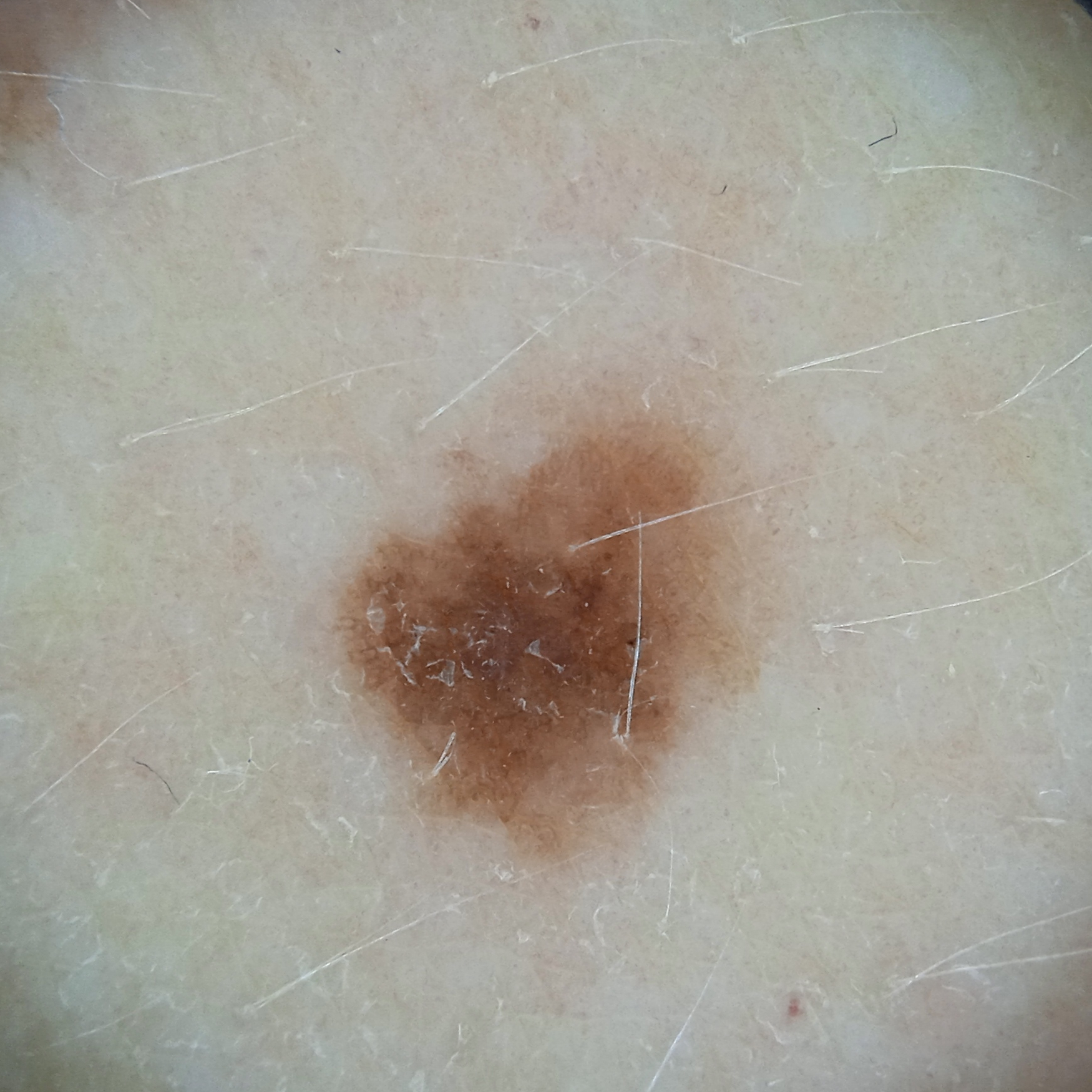* risk factors: a personal history of skin cancer
* modality: dermoscopy
* sun reaction: skin reddens with sun exposure
* patient: female, age 50
* nevus count: a moderate number of melanocytic nevi
* size: 5.4 mm
* diagnosis: melanocytic nevus (dermatologist consensus)